A skin lesion imaged with a dermatoscope.
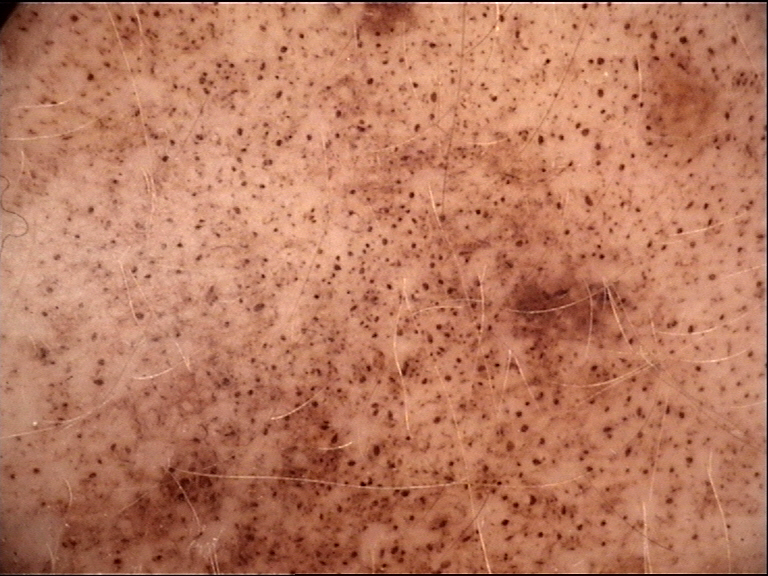This is a banal lesion. The diagnostic label was a congenital junctional nevus.